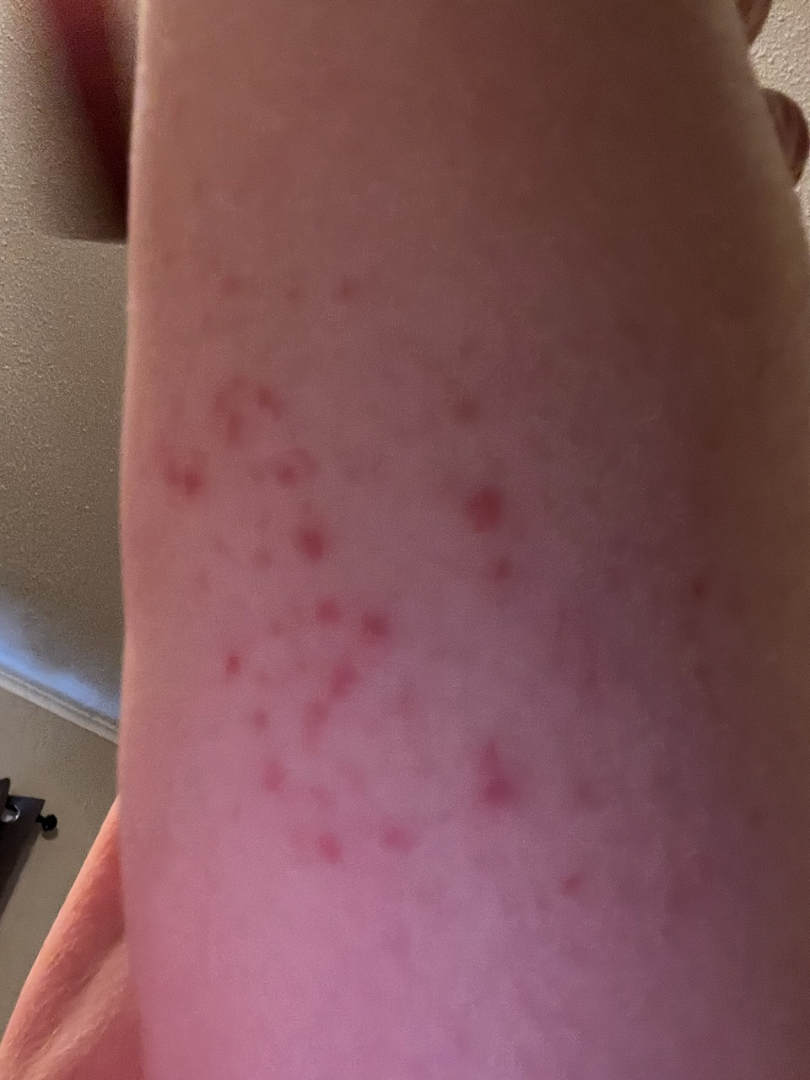Reported duration is less than one week.
The leg is involved.
Skin tone: Fitzpatrick III; lay graders estimated Monk skin tone scale 2.
Self-categorized by the patient as a rash.
The photograph is a close-up of the affected area.
The lesion is described as raised or bumpy.
Reported lesion symptoms include bothersome appearance.
The reviewing dermatologist's impression was: Folliculitis and Irritant Contact Dermatitis were each considered, in no particular order.